The photograph was taken at a distance. The lesion is described as flat. The patient is a female aged 50–59. The patient reported no relevant symptoms from the lesion — 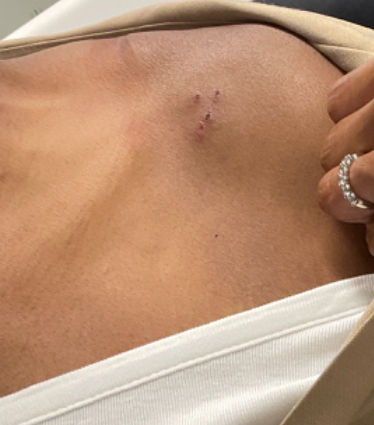Findings:
- diagnostic considerations: most consistent with Eczema; also raised was Herpes Simplex